Dermoscopy of a skin lesion.
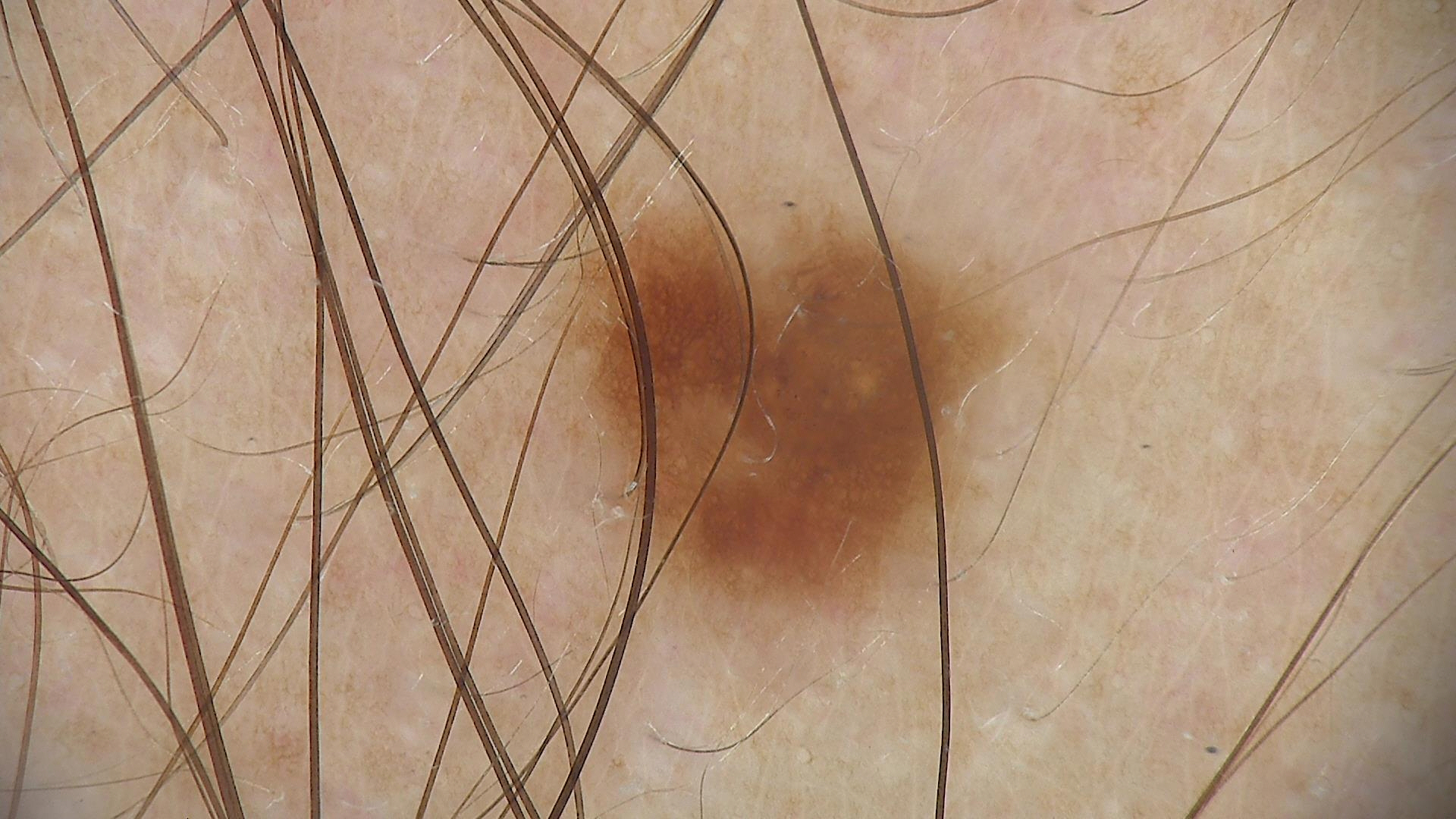Labeled as a benign lesion — a dysplastic junctional nevus.